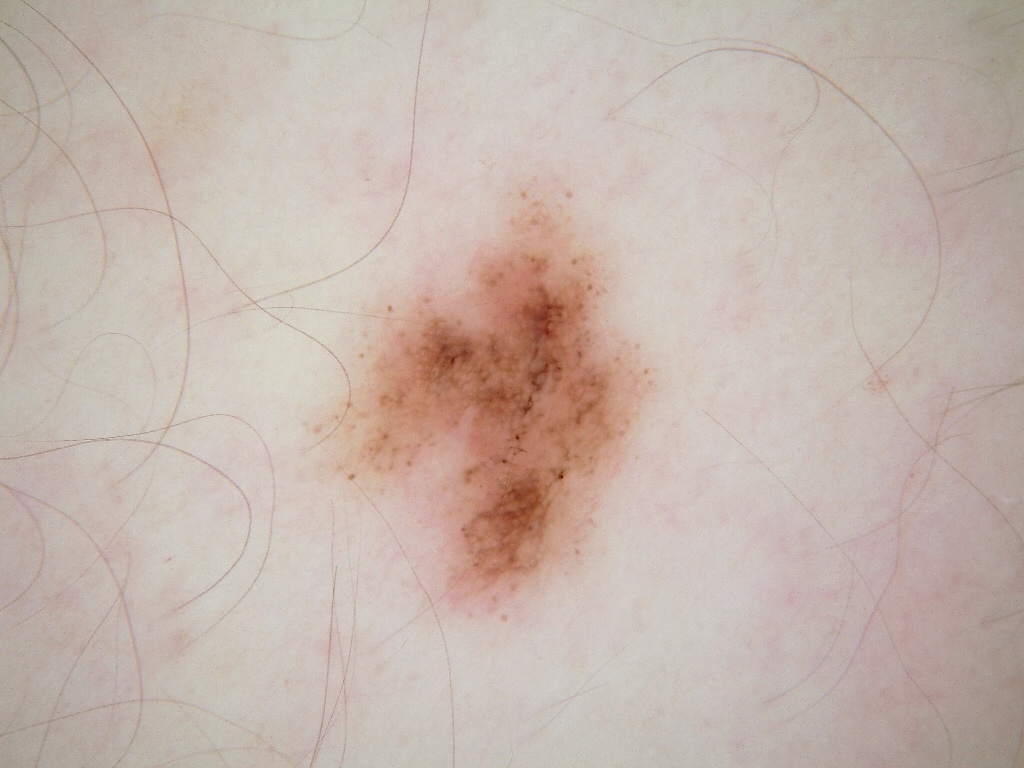Q: Patient demographics?
A: female, aged 23 to 27
Q: How was this image acquired?
A: dermatoscopic image of a skin lesion
Q: Where is the lesion located?
A: x1=299 y1=161 x2=664 y2=631
Q: What dermoscopic features are present?
A: globules and pigment network; absent: milia-like cysts, negative network, and streaks
Q: What did the assessment conclude?
A: a melanocytic nevus, a benign skin lesion